A smartphone photograph of a skin lesion. A subject 77 years of age: 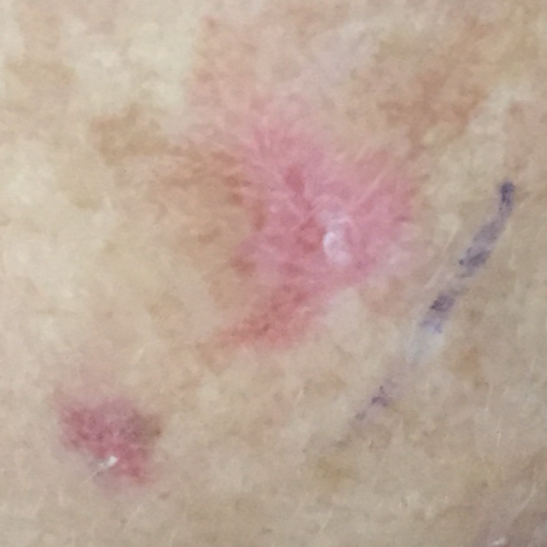| feature | finding |
|---|---|
| location | the face |
| patient-reported symptoms | pain, itching |
| impression | actinic keratosis (clinical consensus) |